Close-up view:
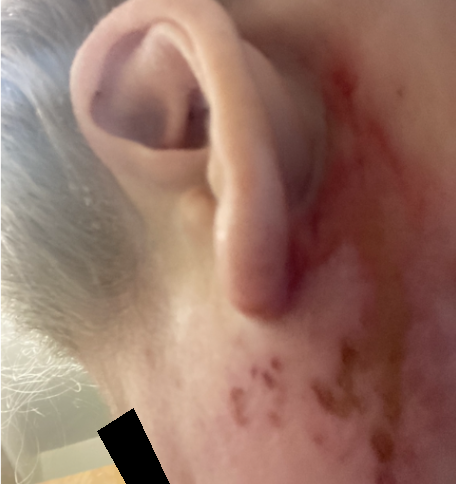Q: Could the case be diagnosed?
A: unable to determine